A skin lesion imaged with a dermatoscope: 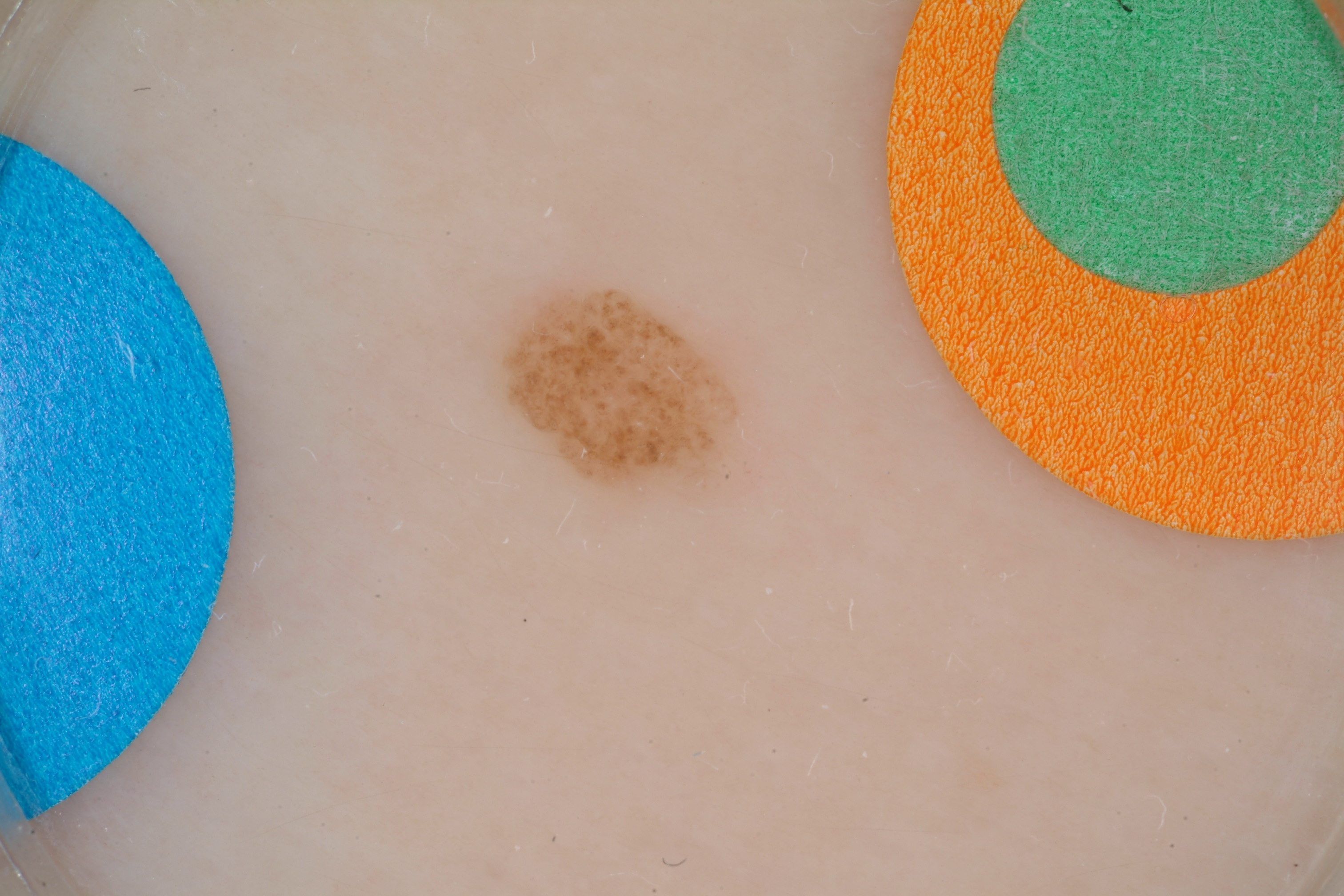The dermoscopic pattern shows milia-like cysts.
With coordinates (x1, y1, x2, y2), the lesion occupies the region <box>491, 284, 747, 503</box>.
The clinical diagnosis was a melanocytic nevus, a benign lesion.